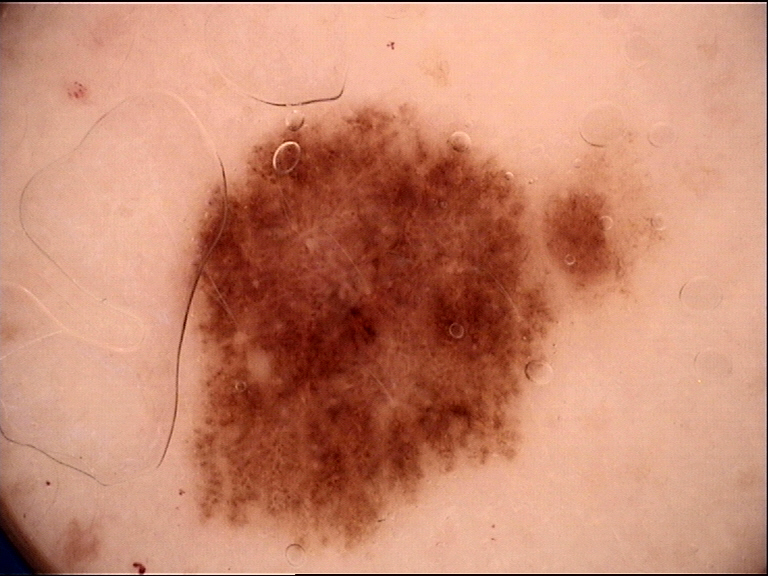{
  "diagnosis": {
    "name": "dysplastic junctional nevus",
    "code": "jd",
    "malignancy": "benign",
    "super_class": "melanocytic",
    "confirmation": "expert consensus"
  }
}